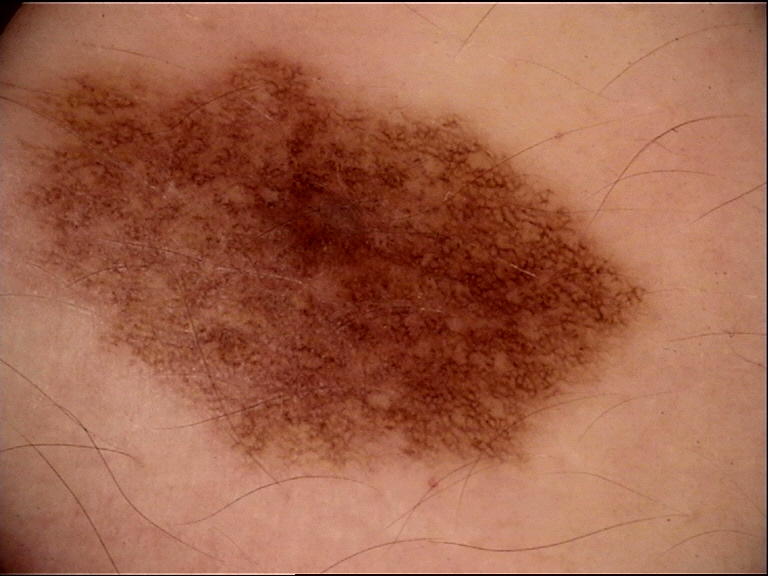modality: dermoscopy
diagnostic label: dysplastic junctional nevus (expert consensus)